Female contributor, age 40–49; this is a close-up image; the front of the torso is involved: 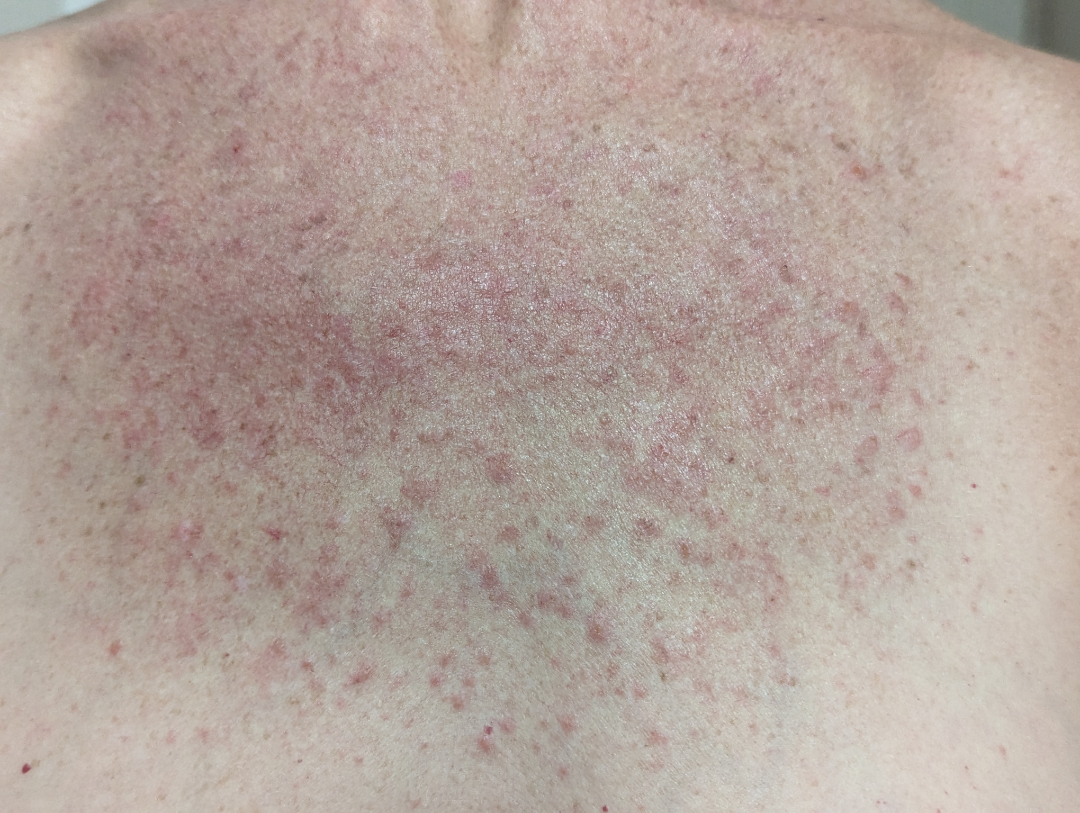differential = the favored diagnosis is Photodermatitis; also consider Acute dermatitis, NOS.